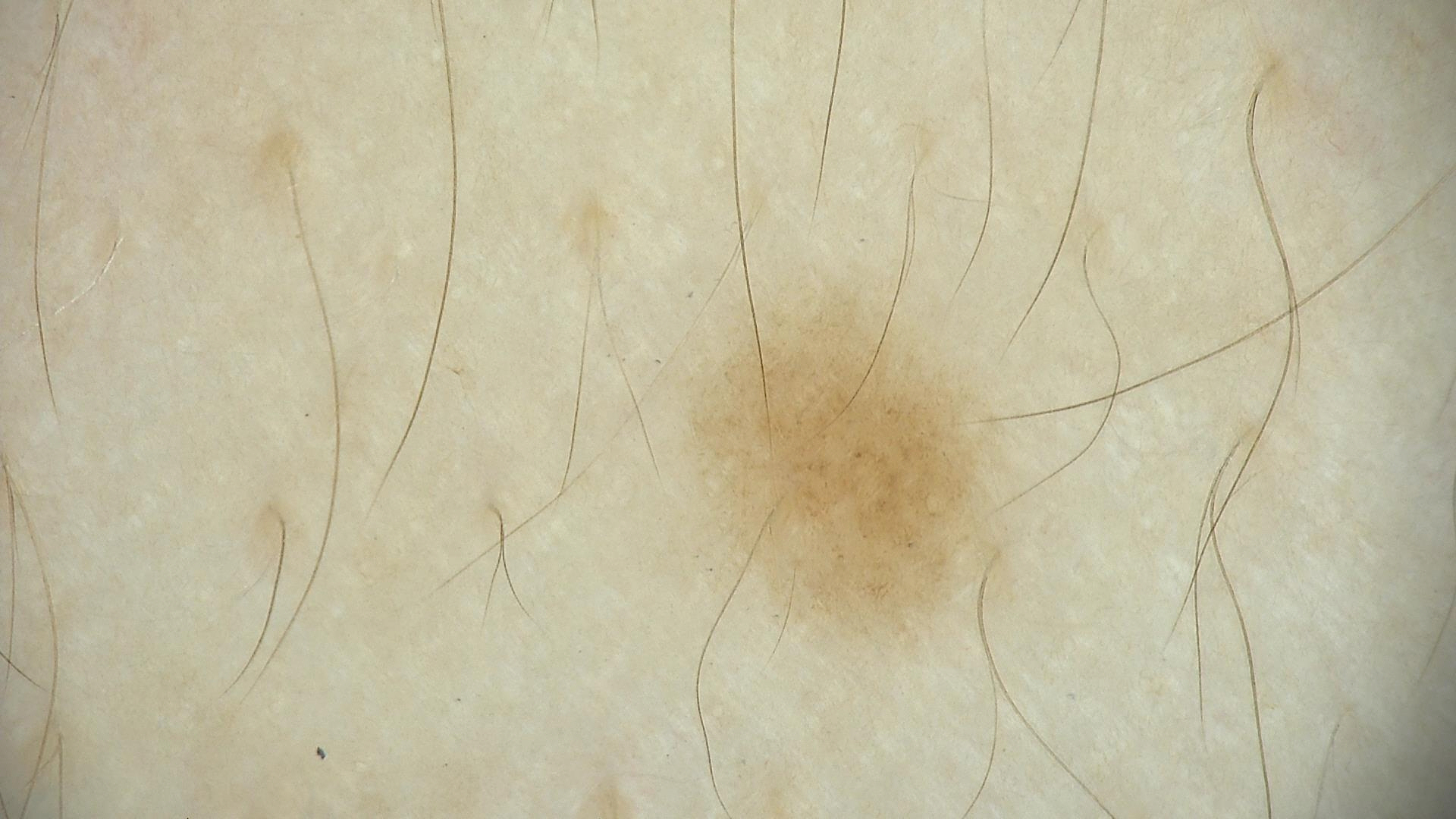A skin lesion imaged with a dermatoscope. Labeled as a benign lesion — a dysplastic junctional nevus.